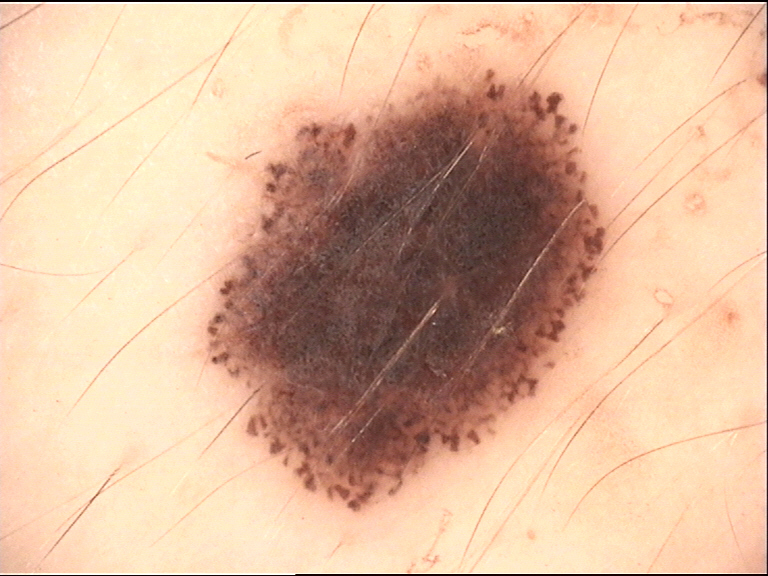{"diagnosis": {"name": "dysplastic junctional nevus", "code": "jd", "malignancy": "benign", "super_class": "melanocytic", "confirmation": "expert consensus"}}